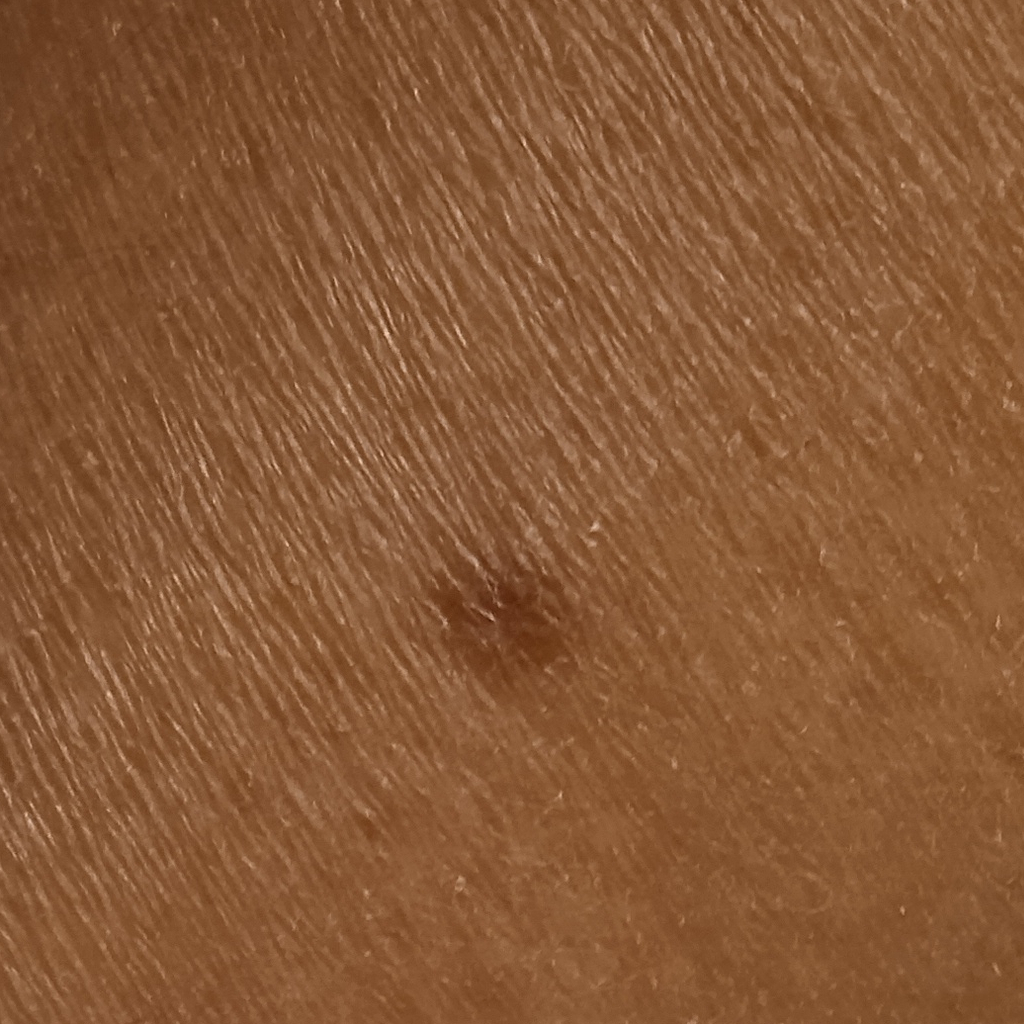Case summary:
Collected as part of a research study, without a referral diagnosis. The patient describes having a moderate number of moles. A female patient 58 years old. The patient says their skin tans without first burning. The patient reports a personal history of cancer, a personal history of skin cancer, a family history of skin cancer, no sunbed use, and no prior organ transplant. A macroscopic clinical photograph of a skin lesion. The lesion is located on a leg. Measuring roughly 5.2 mm.
Conclusion:
The dermatologists' assessment was a dermatofibroma.